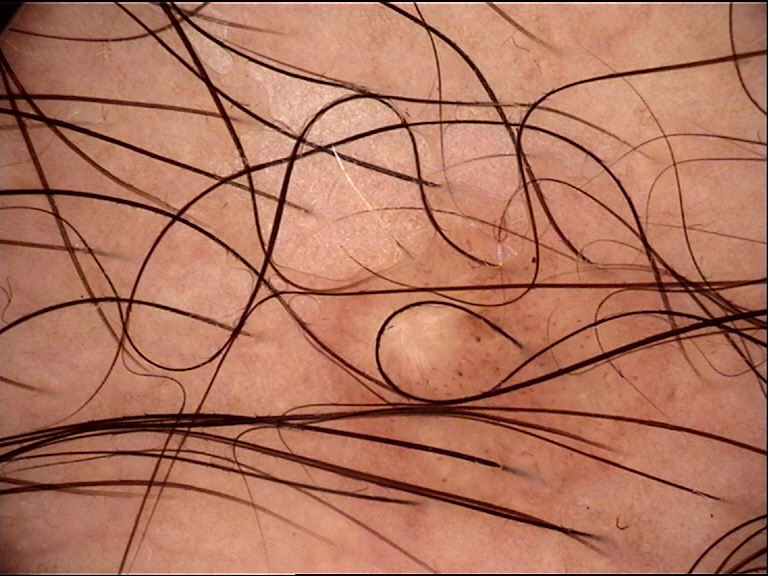class = dermal nevus (expert consensus)